A female patient in their 70s.
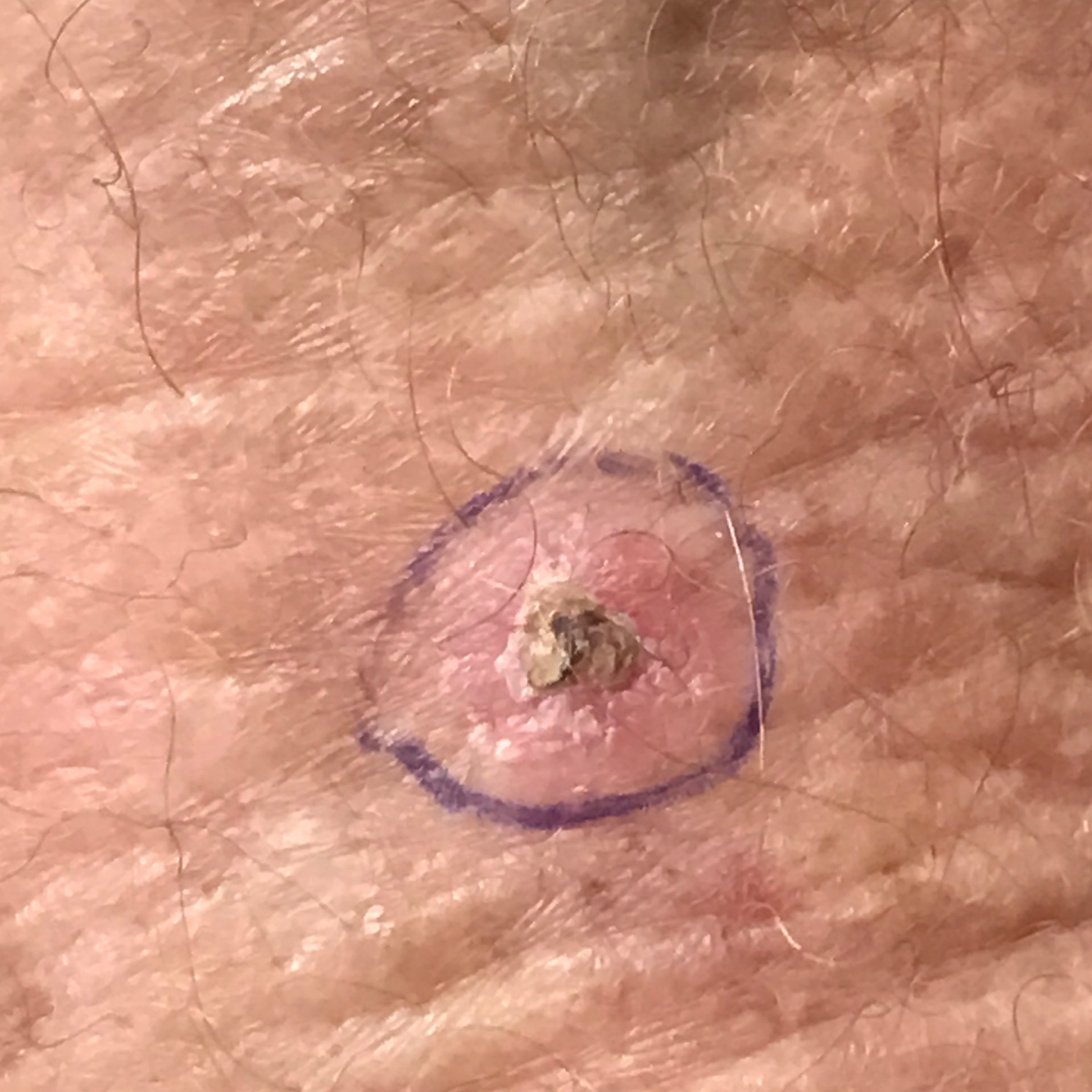Q: What symptoms does the patient report?
A: itching, elevation / no pain, no bleeding
Q: What is the diagnosis?
A: actinic keratosis (biopsy-proven)